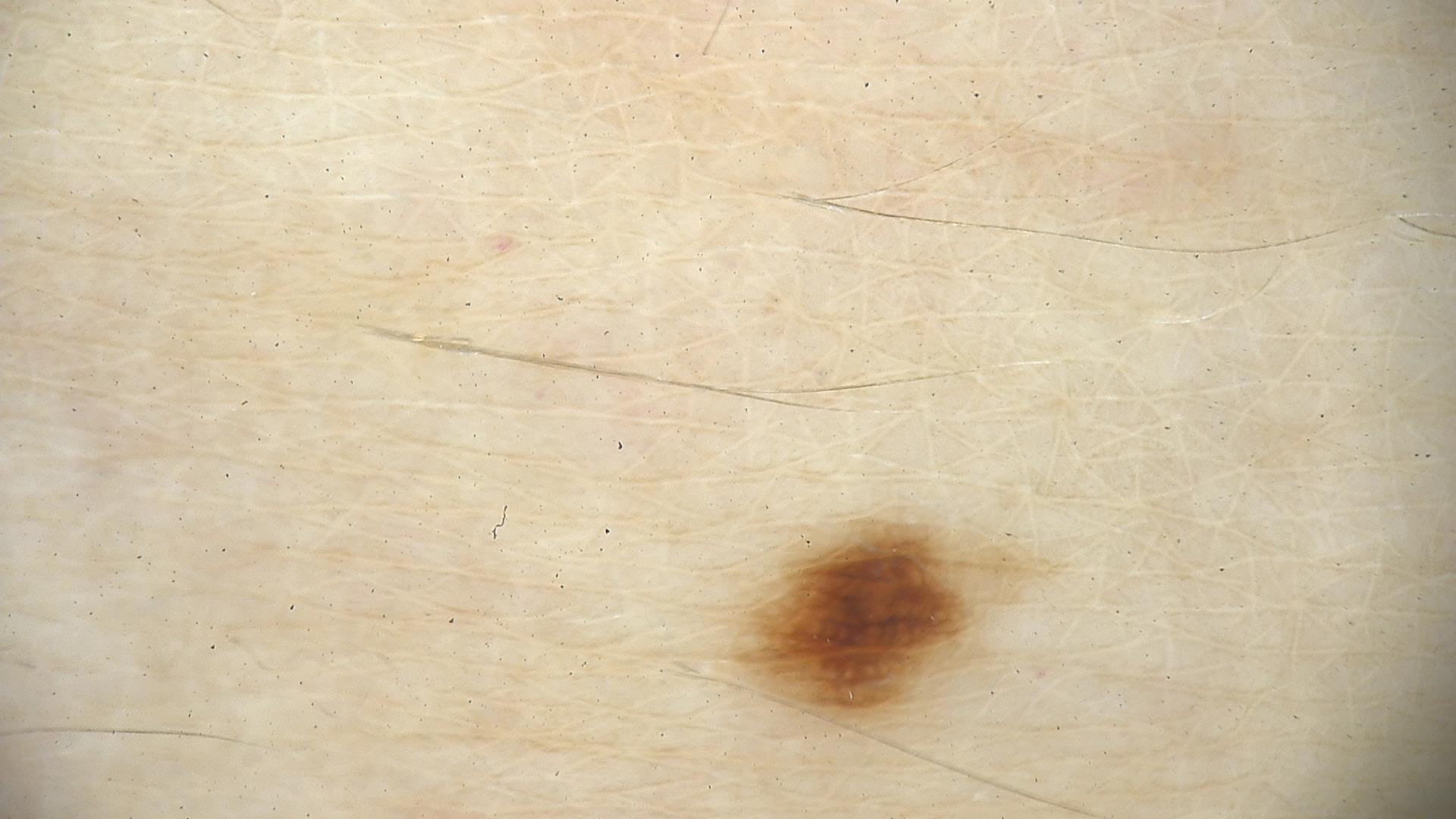Impression: Classified as a dysplastic junctional nevus.